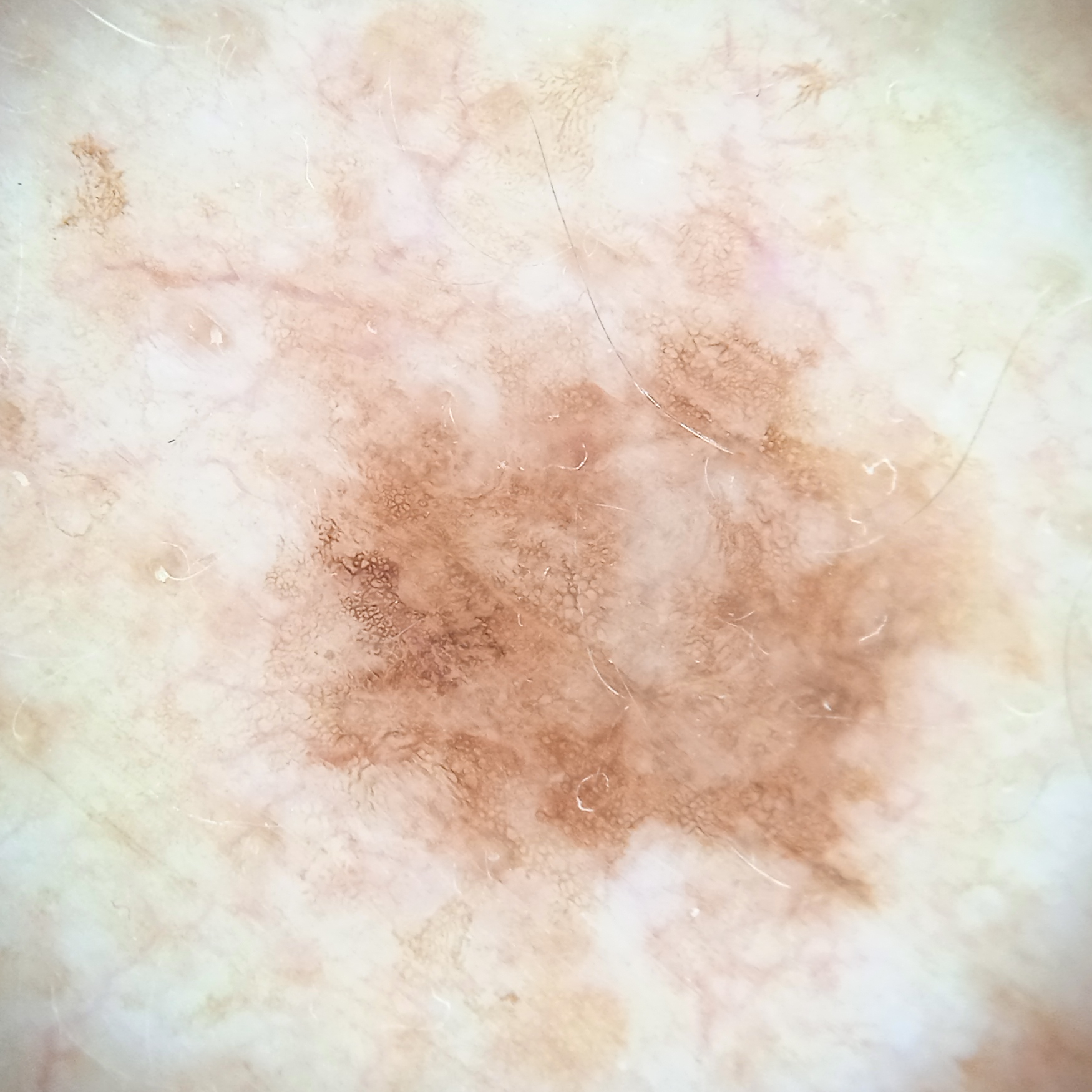The reviewing dermatologists could not reach a confident diagnosis. Case:
- risk factors — a personal history of cancer, a family history of skin cancer
- nevus count — few melanocytic nevi overall
- clinical context — research study (no referral diagnosis)
- modality — dermoscopic image
- patient — male, aged 81
- sun reaction — skin reddens with sun exposure
- location — the back
- diameter — 8 mm